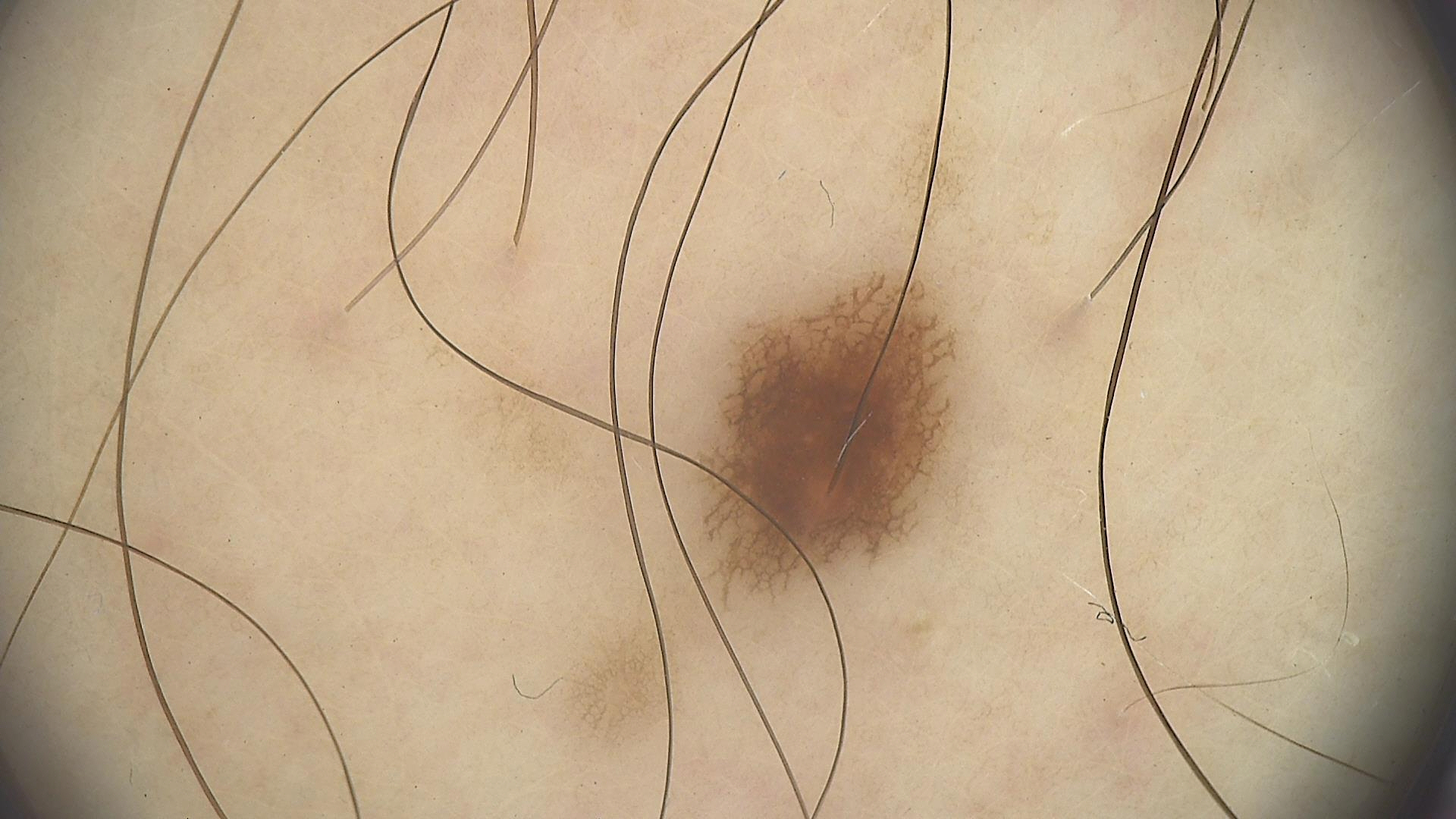A dermoscopic photograph of a skin lesion. Consistent with a benign lesion — a dysplastic junctional nevus.